The contributor is 40–49, female; this image was taken at a distance; no associated systemic symptoms reported; no relevant lesion symptoms reported; the lesion involves the leg; the condition has been present for about one day; the patient described the issue as a rash; the patient reports the lesion is raised or bumpy:
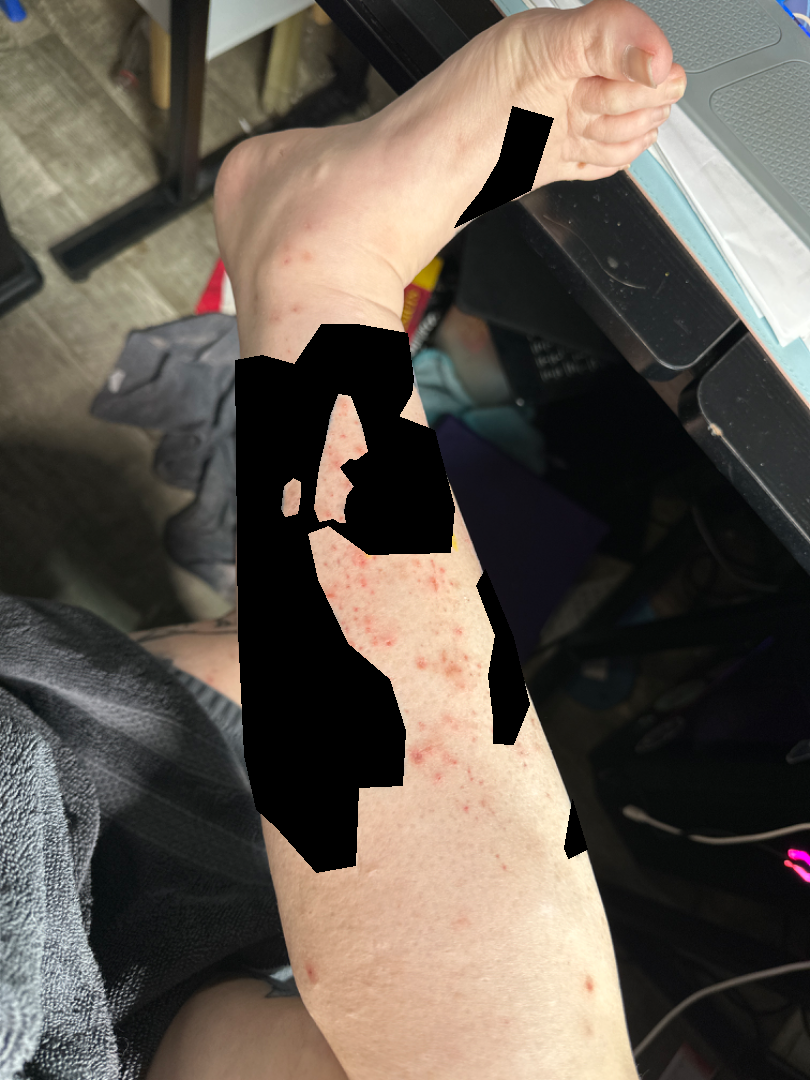Impression: Pigmented purpuric eruption (leading); Leukocytoclastic Vasculitis (possible).